A dermoscopic photograph of a skin lesion.
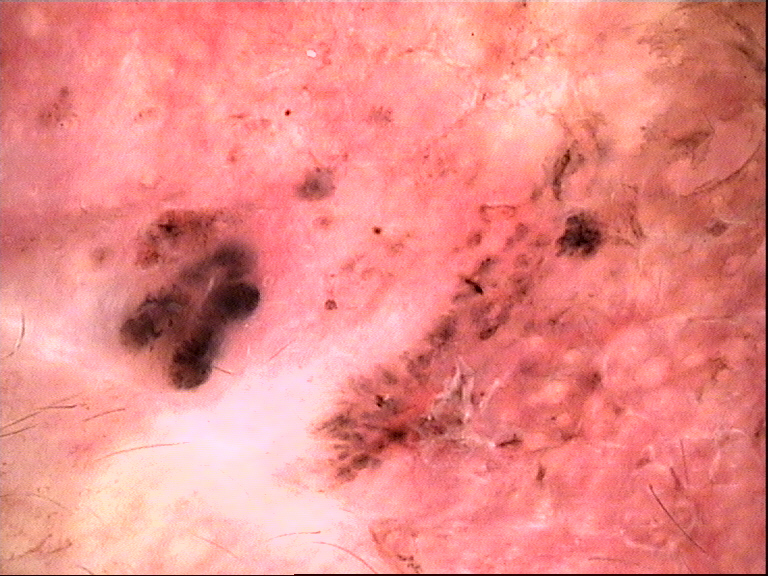Biopsy-confirmed as a keratinocytic, malignant lesion — a basal cell carcinoma.